Male contributor, age 30–39; an image taken at a distance; the affected area is the leg.
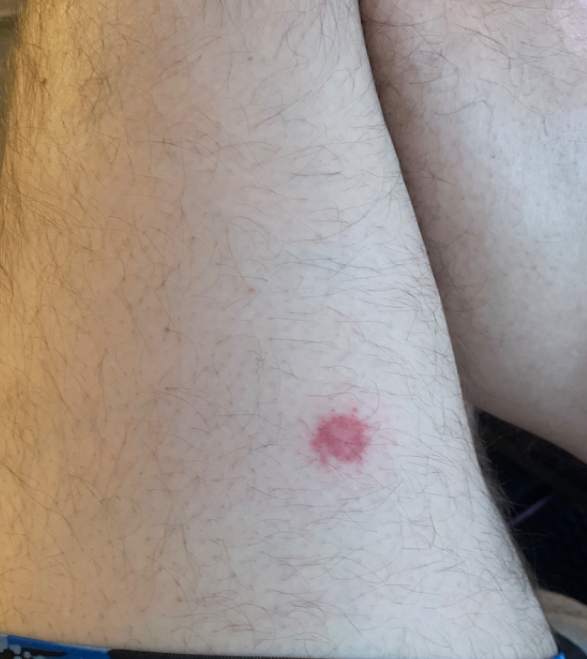<report>
  <symptoms>itching, bothersome appearance</symptoms>
  <duration>less than one week</duration>
  <systemic_symptoms>none reported</systemic_symptoms>
  <differential>
    <tied_lead>Purpura, ecchymoses</tied_lead>
    <unlikely>Pigmented purpuric eruption, Insect Bite, Hemangioma</unlikely>
  </differential>
</report>